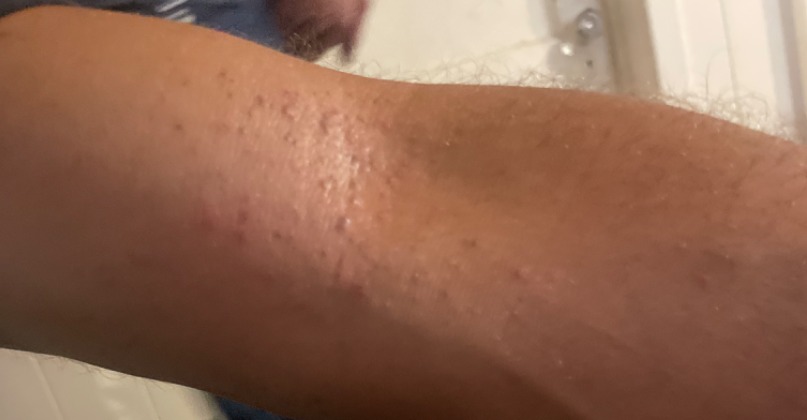The skin findings could not be characterized from the image.
The patient described the issue as a rash.
The lesion is described as raised or bumpy.
No relevant systemic symptoms.
The patient reports the condition has been present for three to twelve months.
This image was taken at an angle.
The patient reports itching.
The affected area is the arm.